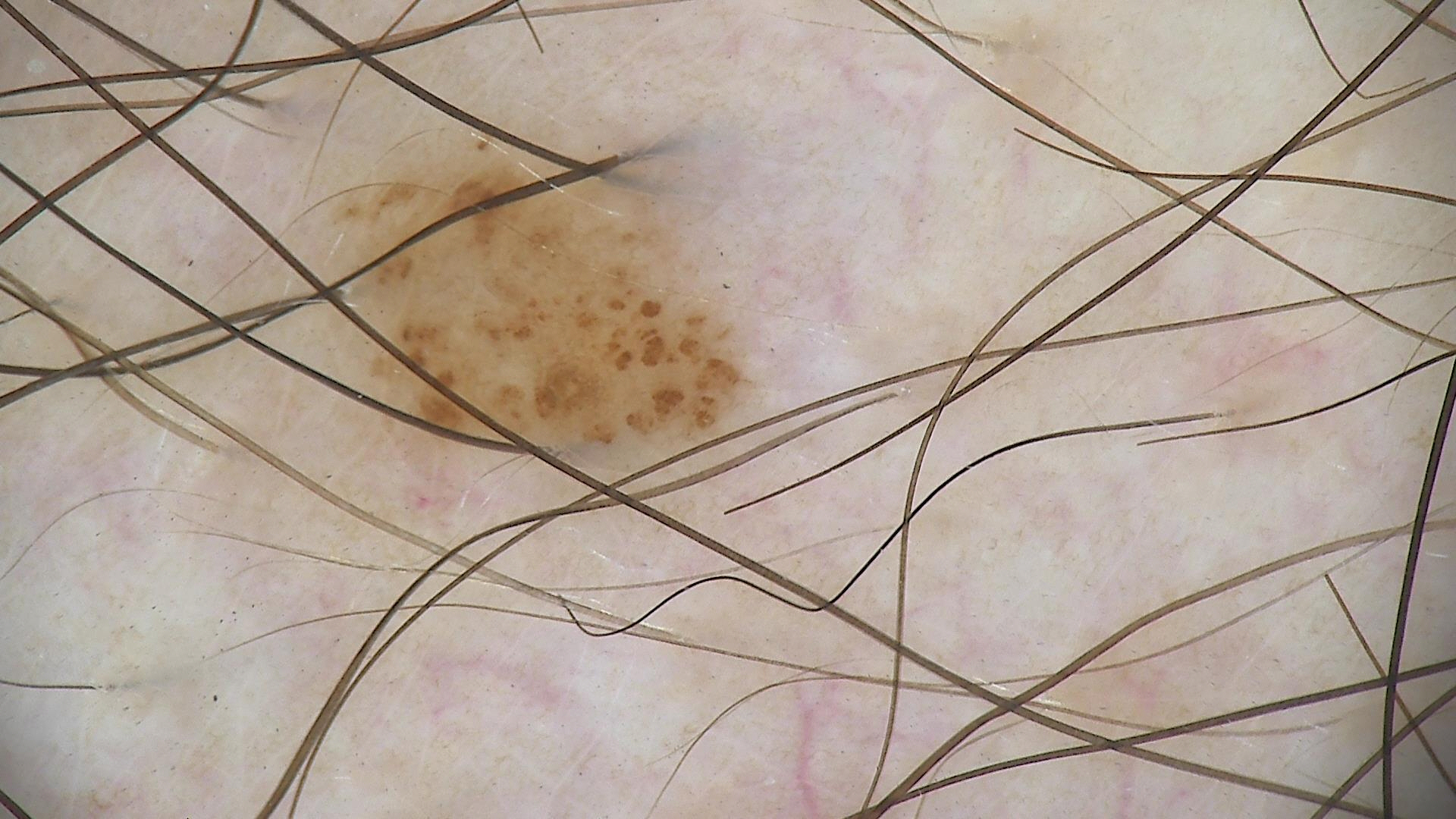image = dermatoscopy | assessment = dysplastic junctional nevus (expert consensus).